The front of the torso is involved. Present for one to four weeks. The patient described the issue as a rash. The lesion is associated with enlargement and itching. The patient notes associated mouth sores. Female subject, age 18–29. A close-up photograph. The patient notes the lesion is rough or flaky and raised or bumpy — 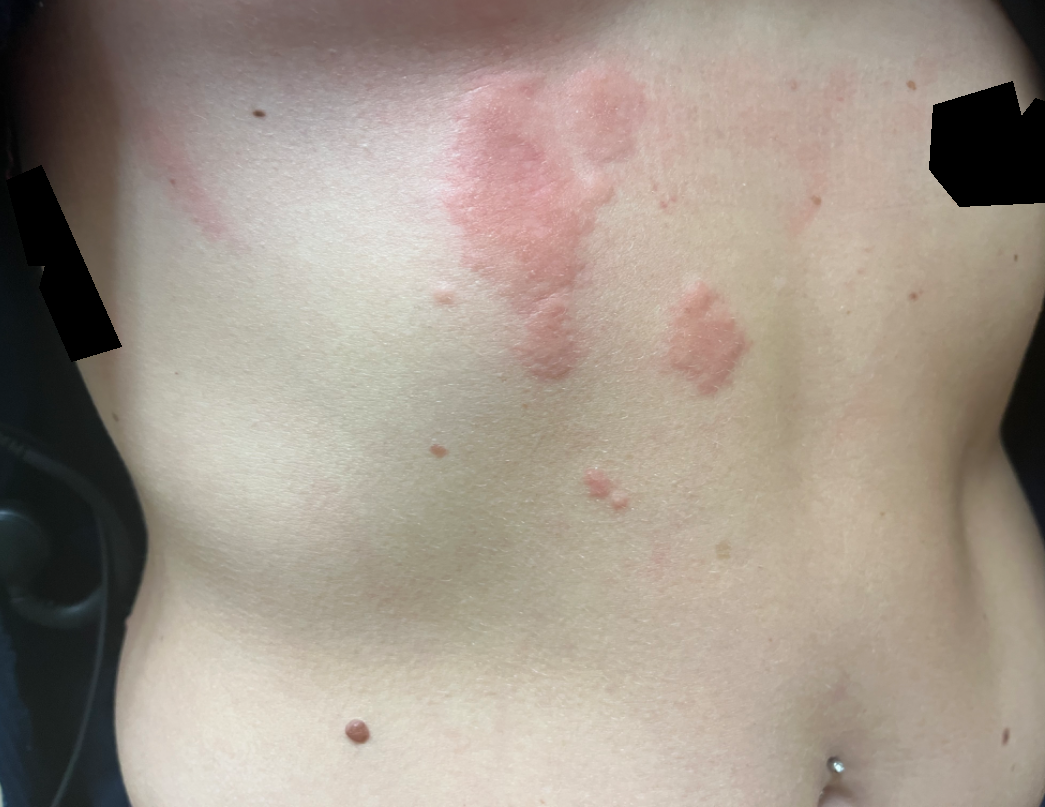Q: What is the dermatologist's impression?
A: consistent with Urticaria